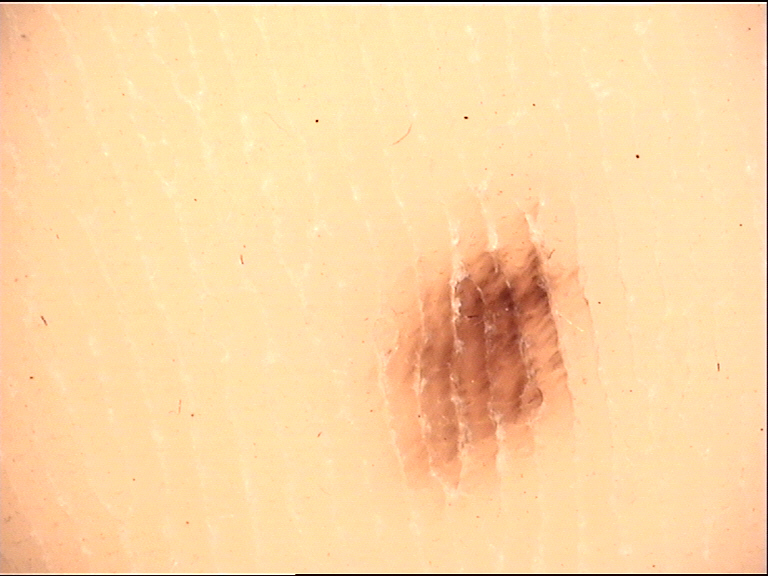  diagnosis:
    name: acral junctional nevus
    code: ajb
    malignancy: benign
    super_class: melanocytic
    confirmation: expert consensus